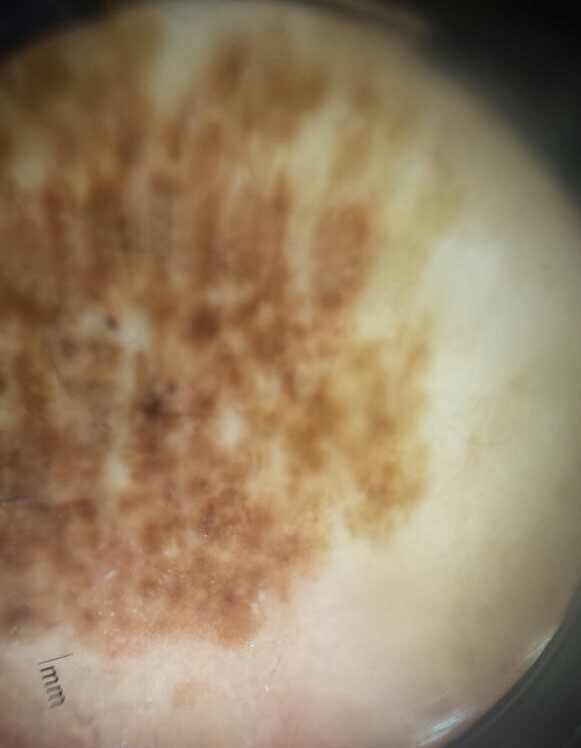The diagnostic label was a congenital dysplastic compound nevus.